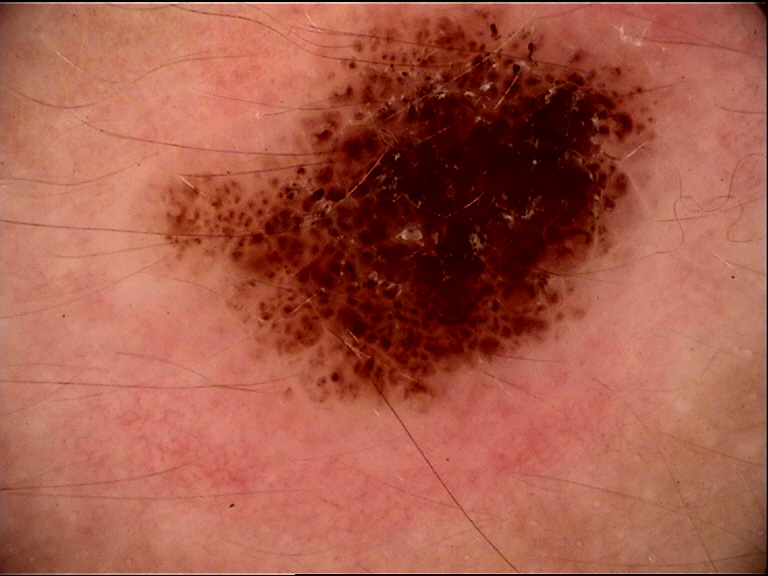assessment=compound nevus (expert consensus)